A clinical photograph of a skin lesion · the patient reports a history of sunbed use · the patient says their skin reddens with sun exposure · numerous moles by the patient's own estimate · a female patient 26 years old.
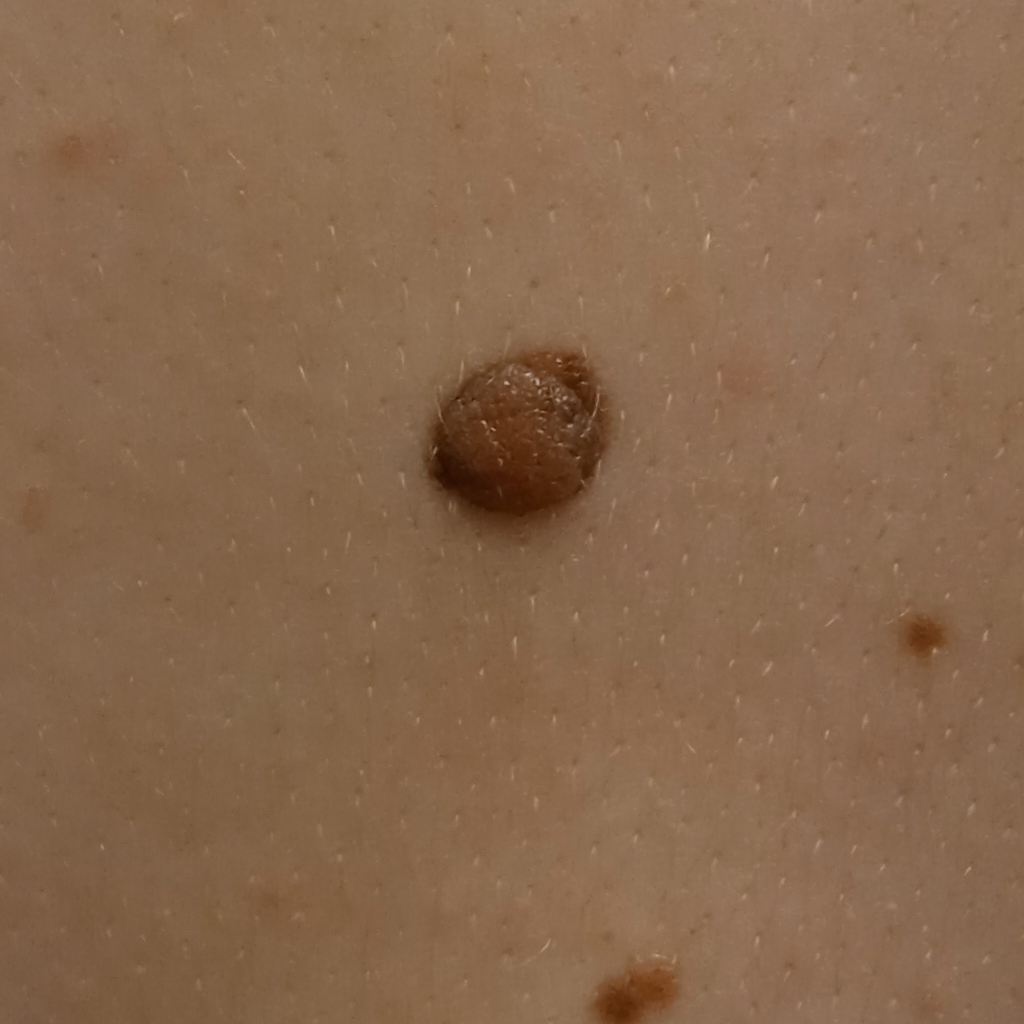Findings: Located on the back. Measuring roughly 8.9 mm. Impression: Dermatologist review favored a melanocytic nevus.